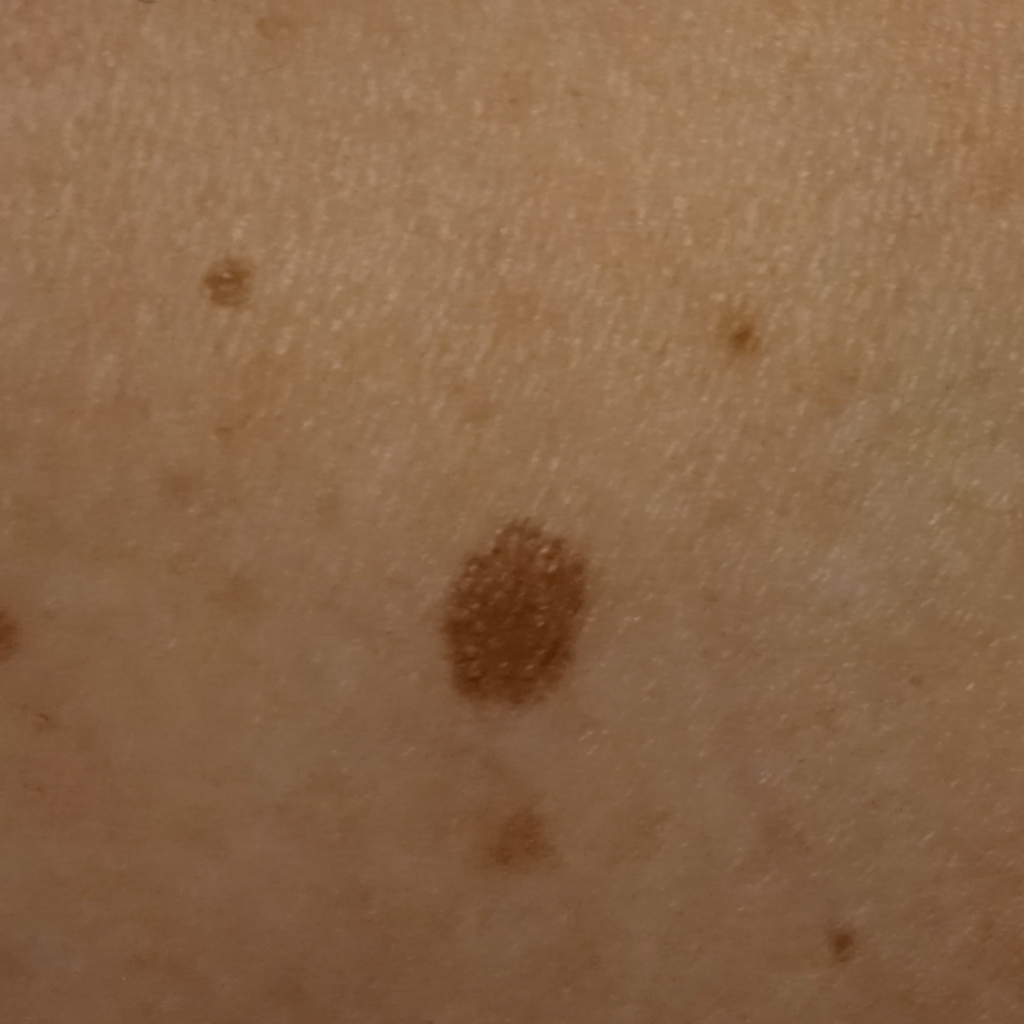clinical context=clinical suspicion of melanocytic nevus | image type=clinical photograph | nevus count=a moderate number of melanocytic nevi | patient=female, 59 years of age | anatomic site=an arm | size=6.7 mm | pathology=atypical (dysplastic) nevus — biopsy-proven.